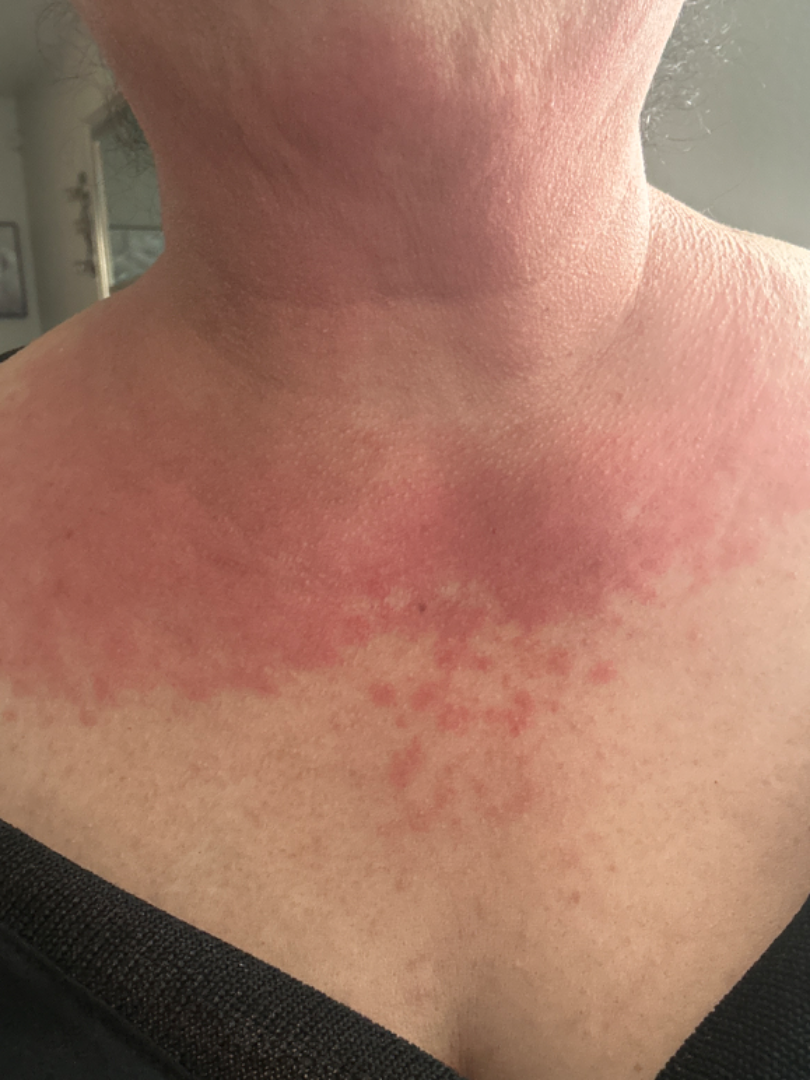| key | value |
|---|---|
| contributor | female, age 50–59 |
| affected area | leg, head or neck and arm |
| symptom duration | less than one week |
| shot type | close-up |
| lesion texture | raised or bumpy and flat |
| diagnostic considerations | single-reviewer assessment: the primary impression is Cutaneous lupus; also consider Dermatomyositis; possibly Allergic Contact Dermatitis |